A dermoscopic image of a skin lesion.
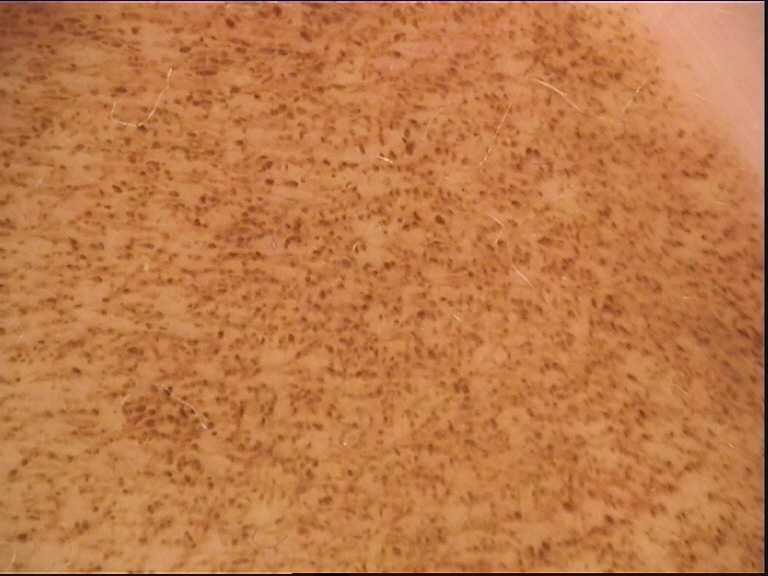<case>
  <lesion_type>
    <main_class>banal</main_class>
    <pattern>junctional</pattern>
  </lesion_type>
  <diagnosis>
    <name>congenital junctional nevus</name>
    <code>cjb</code>
    <malignancy>benign</malignancy>
    <super_class>melanocytic</super_class>
    <confirmation>expert consensus</confirmation>
  </diagnosis>
</case>